The photograph is a close-up of the affected area; the lesion involves the leg; the subject is female — 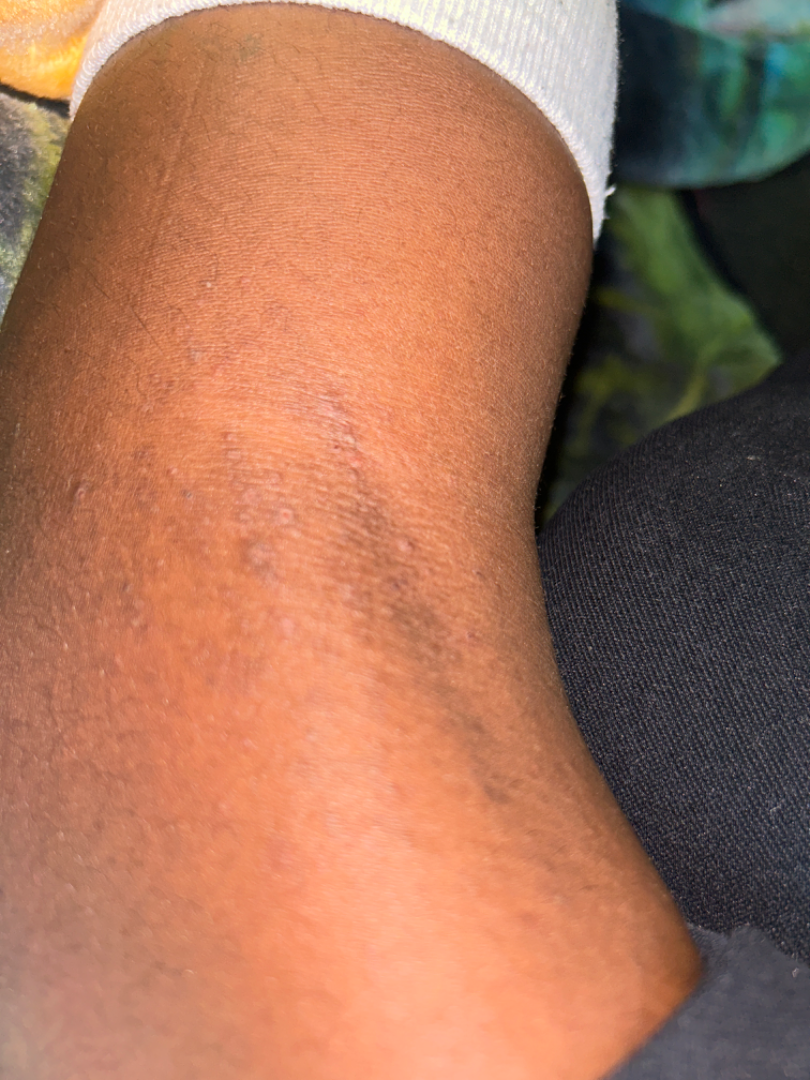– clinical impression — in keeping with Eczema